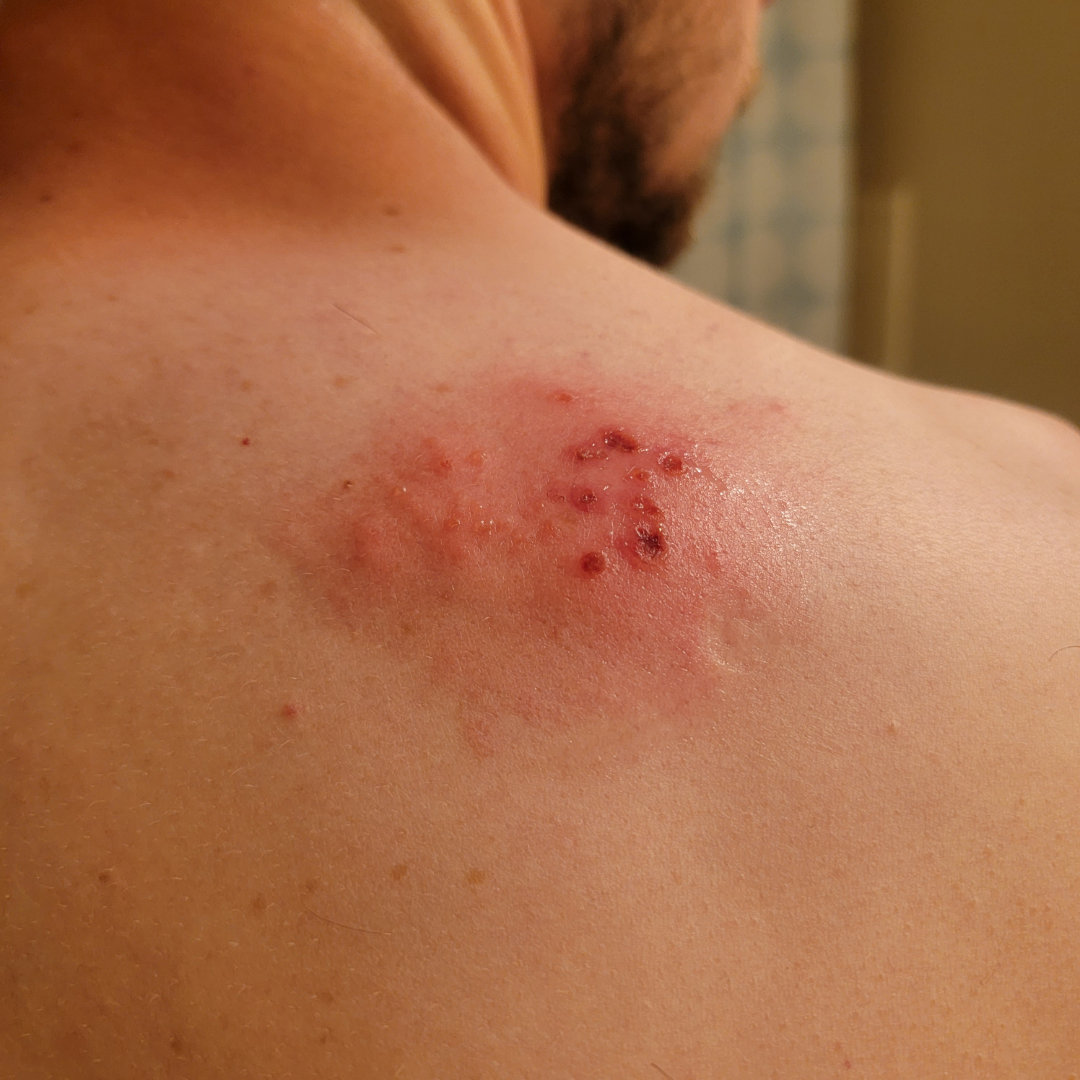assessment=unable to determine
photo taken=close-up
onset=one to four weeks
self-categorized as=a rash
texture=raised or bumpy
body site=back of the torso
lesion symptoms=bothersome appearance, pain, darkening and itching
systemic symptoms=none reported